Skin type II. A smartphone photograph of a skin lesion. History notes prior skin cancer (patient or family), alcohol use, prior malignancy (patient or family), no pesticide exposure, and no tobacco use. A male subject in their 50s: 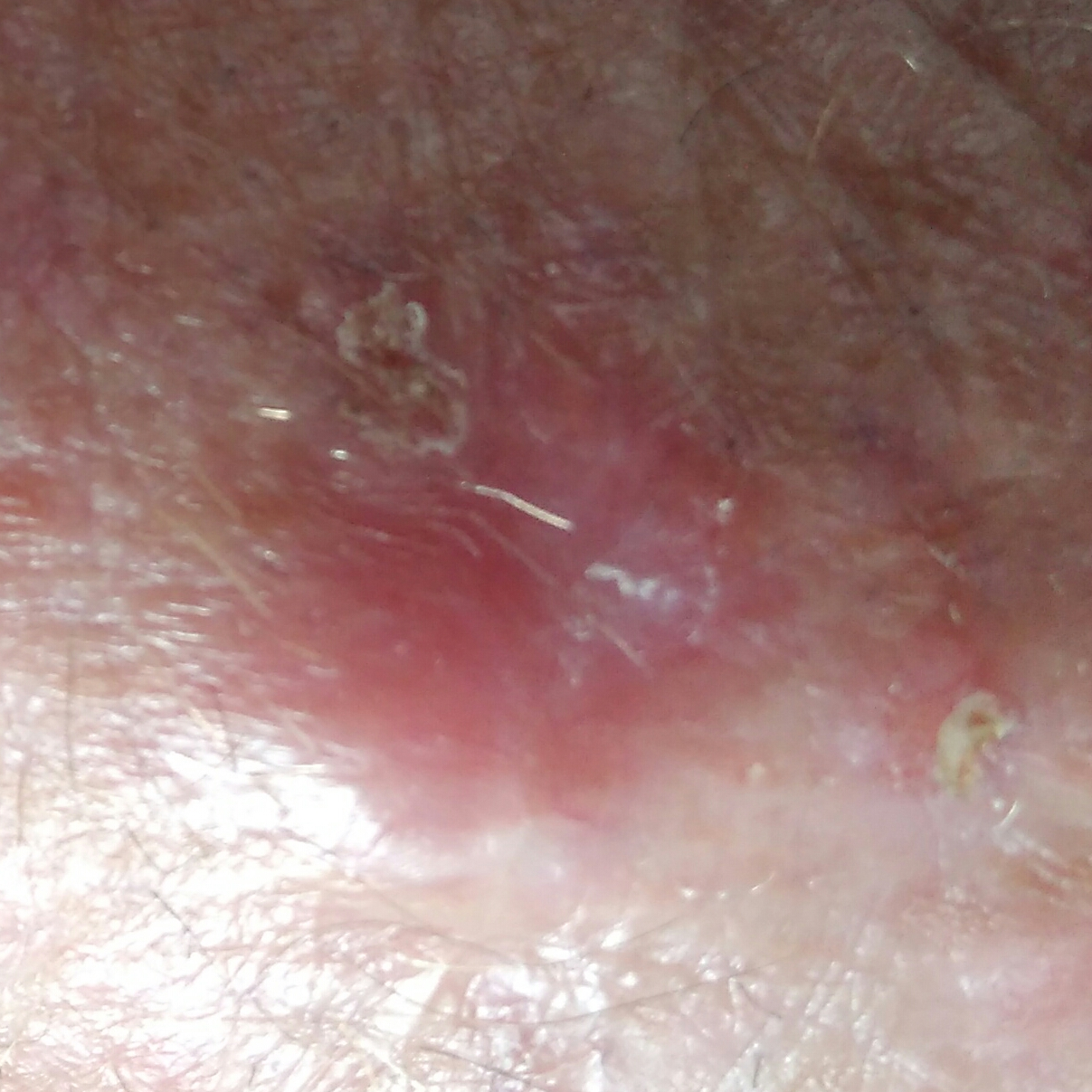anatomic site: a hand
size: 13 × 10 mm
symptoms: itching, elevation / no change in appearance
diagnosis: basal cell carcinoma (biopsy-proven)